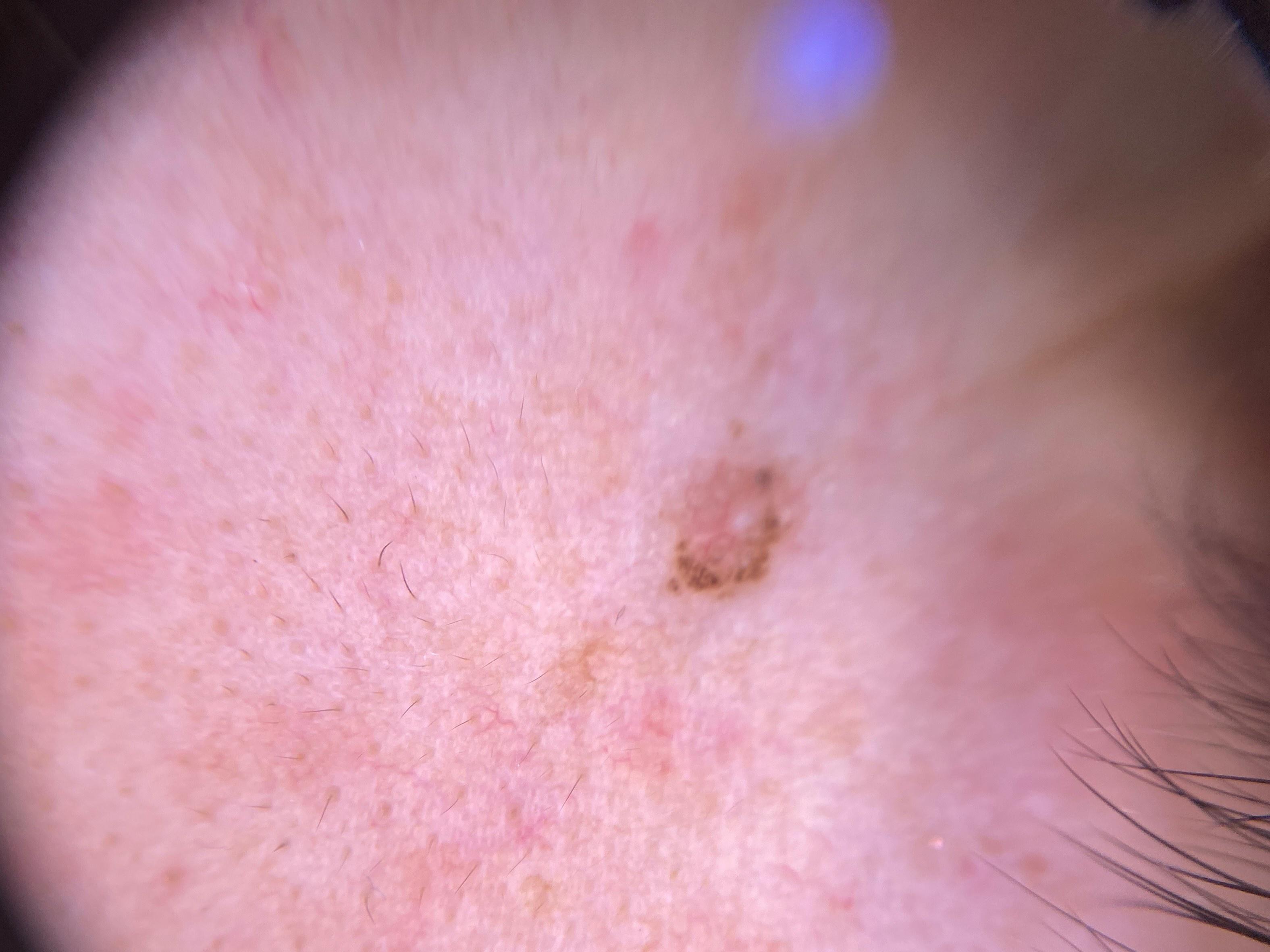Case summary: A male patient approximately 30 years of age. A dermoscopic close-up of a skin lesion. The lesion was found on the head or neck. Conclusion: On biopsy, the diagnosis was a basal cell carcinoma.